A dermoscopic photograph of a skin lesion.
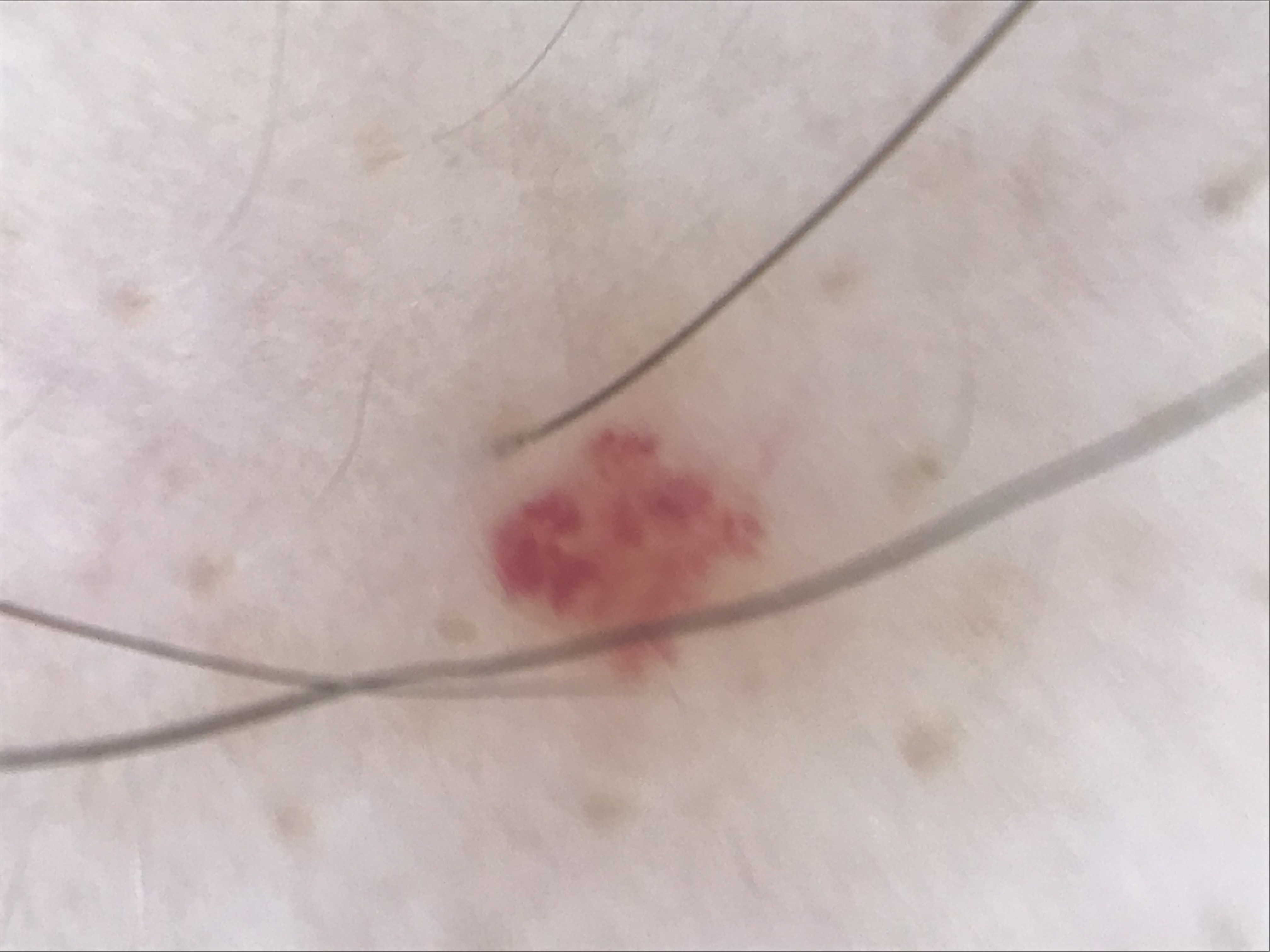Labeled as a benign, vascular lesion — a hemangioma.